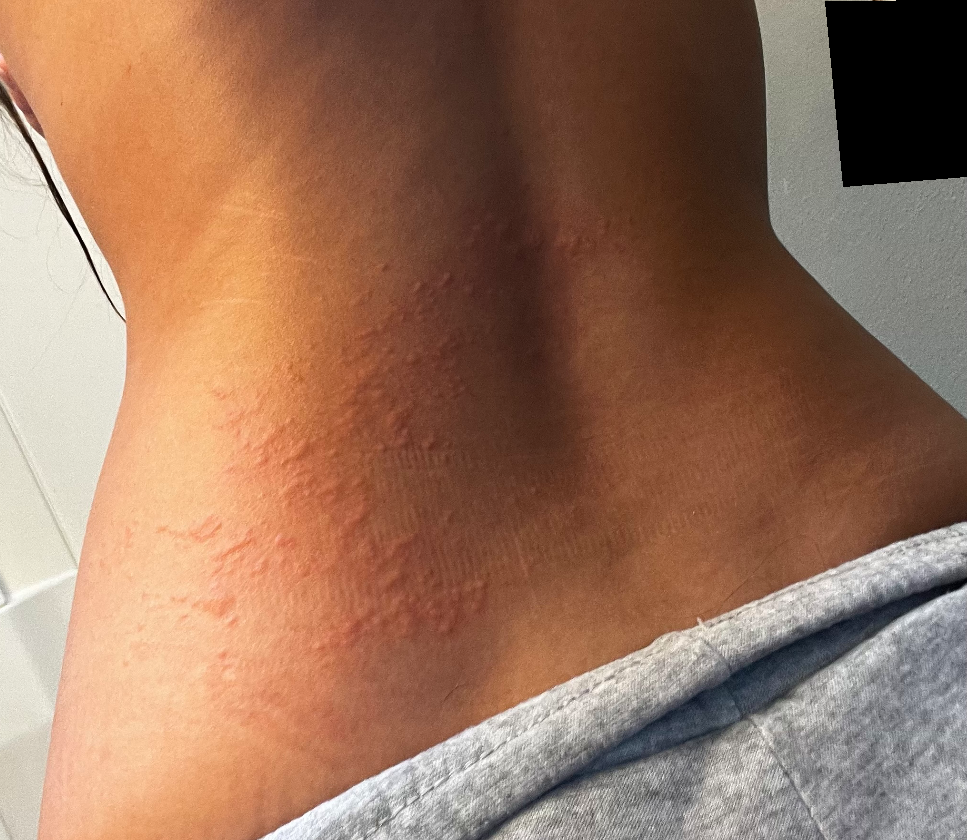Symptoms reported: itching.
A close-up photograph.
The affected area is the back of the torso.
The patient notes the condition has been present for about one day.
The patient notes the lesion is raised or bumpy.
Most consistent with Urticaria; also raised was Allergic Contact Dermatitis.